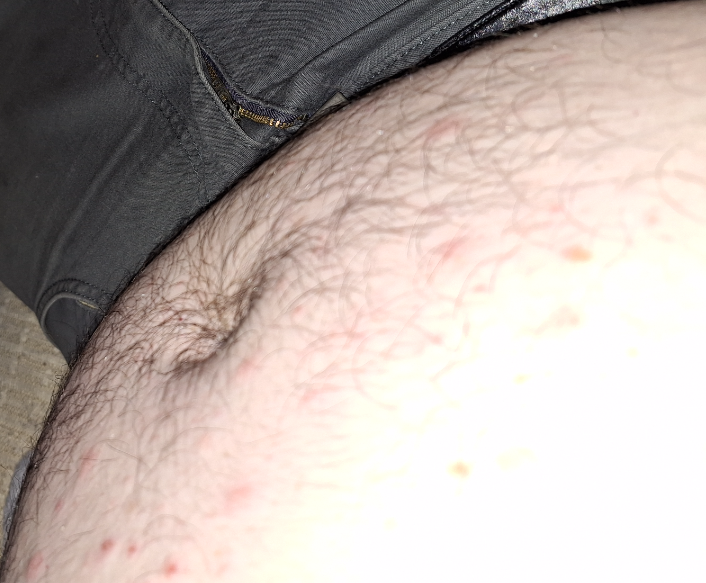Background:
This image was taken at an angle.
Findings:
A single dermatologist reviewed the case: Pityriasis lichenoides, Scabies and Folliculitis were considered with similar weight.